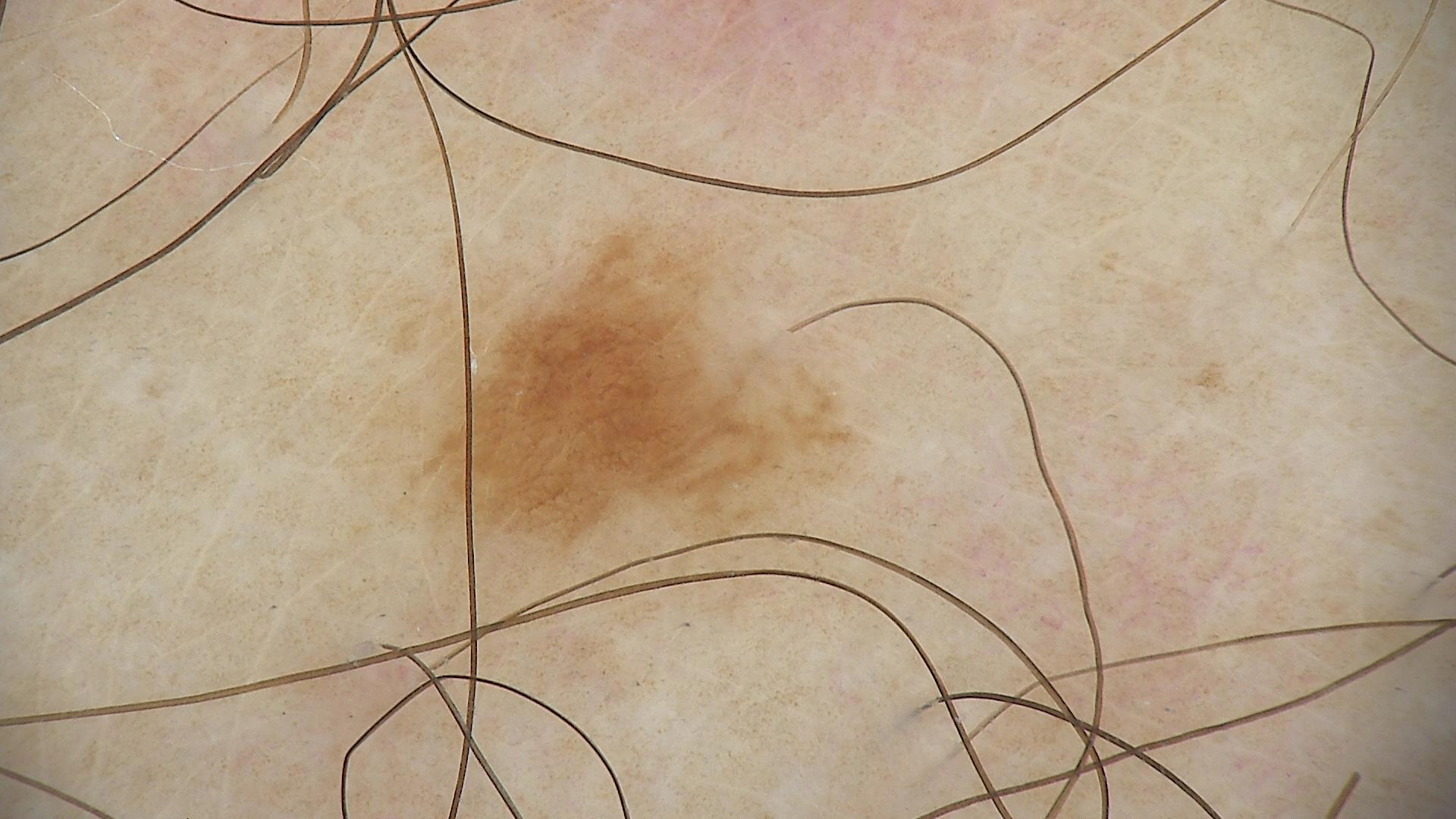Conclusion:
Classified as a benign lesion — a dysplastic junctional nevus.